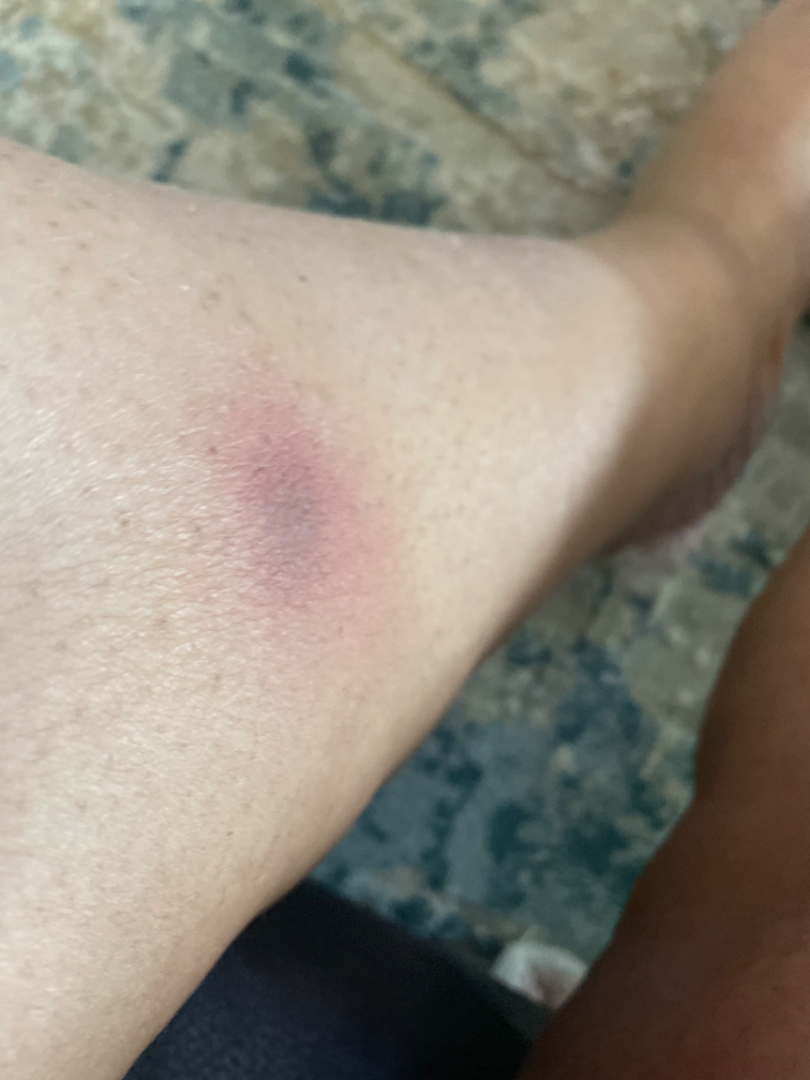Background: The patient reported no relevant symptoms from the lesion. The lesion is described as fluid-filled. This is a close-up image. No constitutional symptoms were reported. The leg is involved. Findings: Single-reviewer assessment: Insect Bite, Lichen planus/lichenoid eruption and Eczema were each considered, in no particular order.